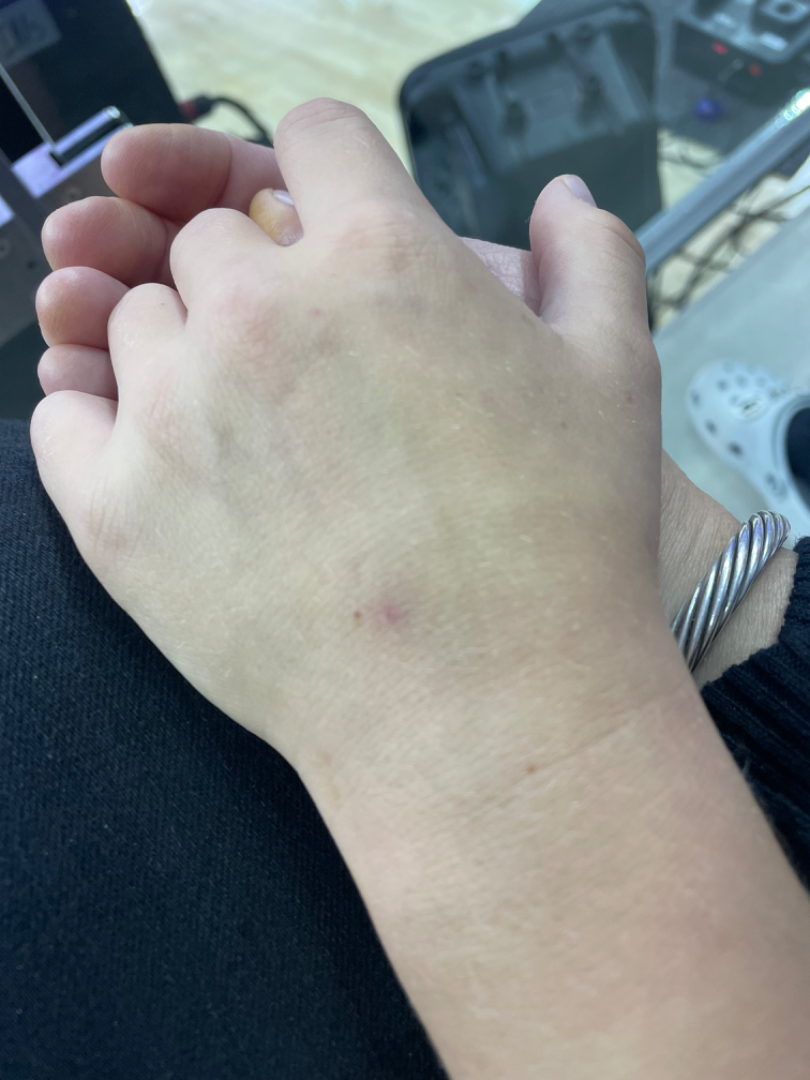skin tone: Fitzpatrick skin type III | present for: more than one year | site: arm | texture: flat | photo taken: close-up | differential diagnosis: Insect Bite and Molluscum Contagiosum were each considered, in no particular order.